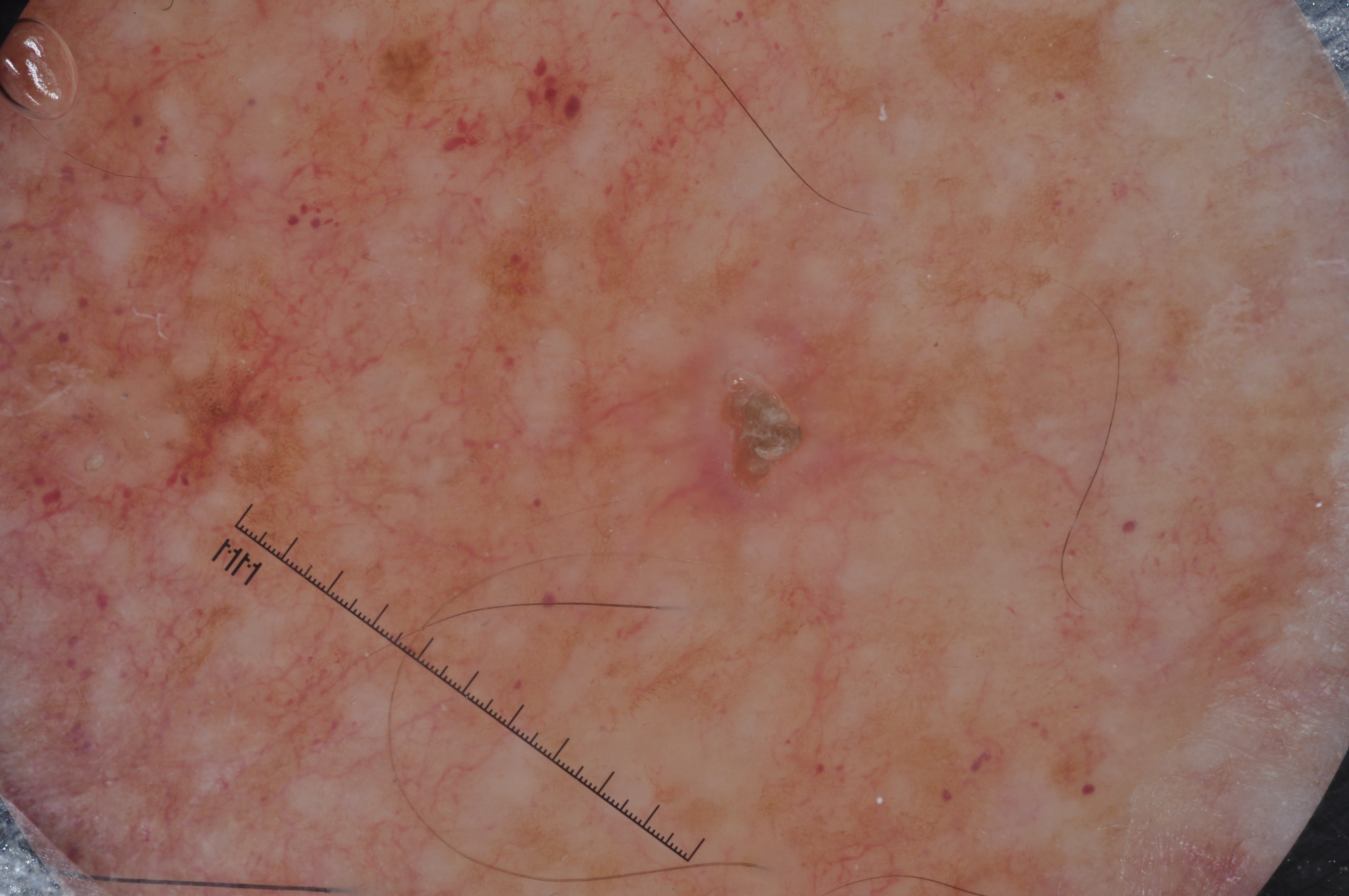A dermoscopy image of a single skin lesion. A male patient, about 50 years old. The lesion occupies roughly 4% of the field. As (left, top, right, bottom), the lesion spans 615, 309, 887, 530. Dermoscopic assessment notes no streaks, pigment network, negative network, or milia-like cysts. Expert review diagnosed this as a seborrheic keratosis.